A female patient in their mid-20s, a dermoscopic view of a skin lesion.
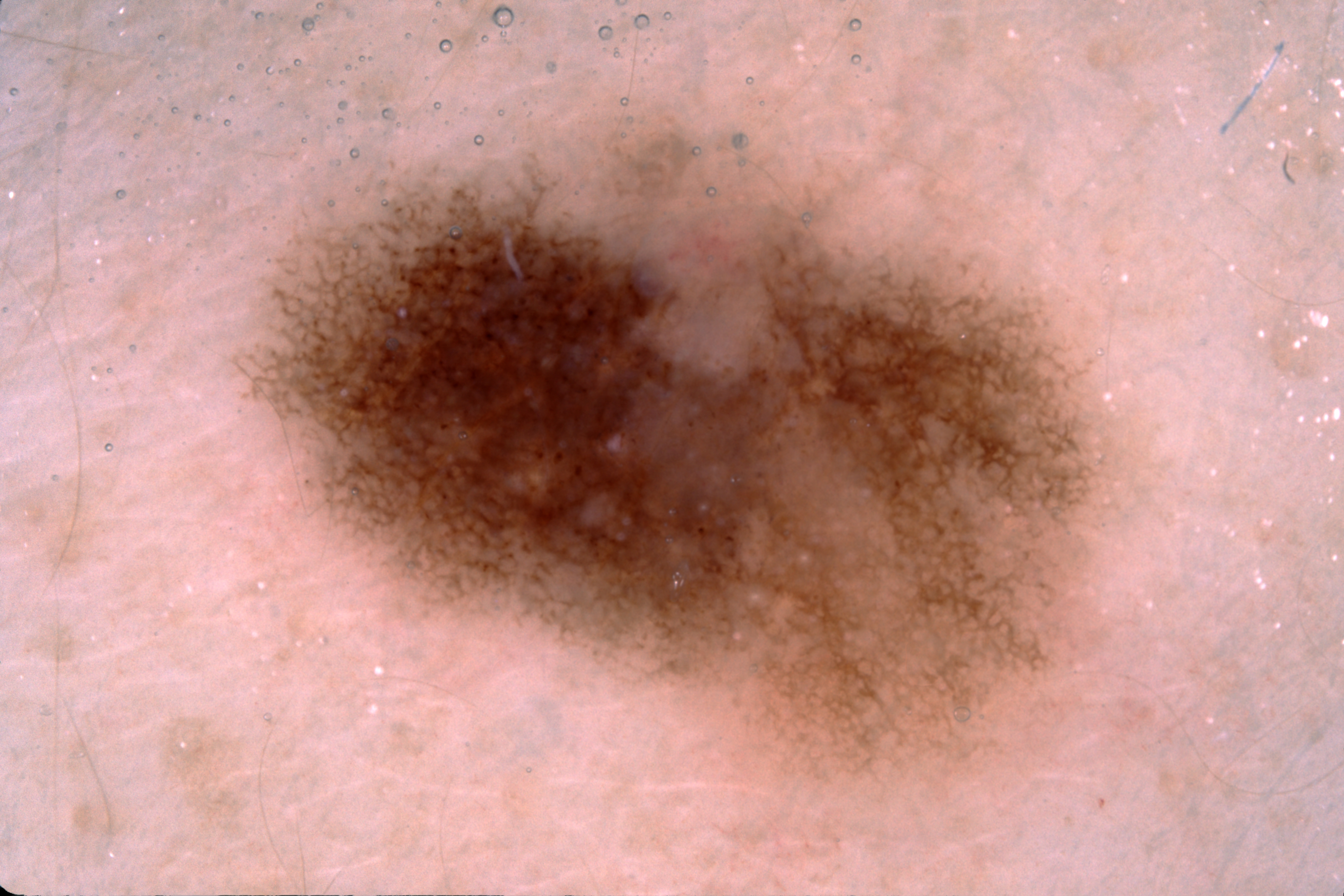{"dermoscopic_features": {"present": ["milia-like cysts", "pigment network"], "absent": ["negative network", "streaks"]}, "lesion_location": {"bbox_xyxy": [232, 107, 1100, 782]}, "lesion_extent": {"approx_field_fraction_pct": 31}, "diagnosis": {"name": "melanocytic nevus", "malignancy": "benign", "lineage": "melanocytic", "provenance": "clinical"}}